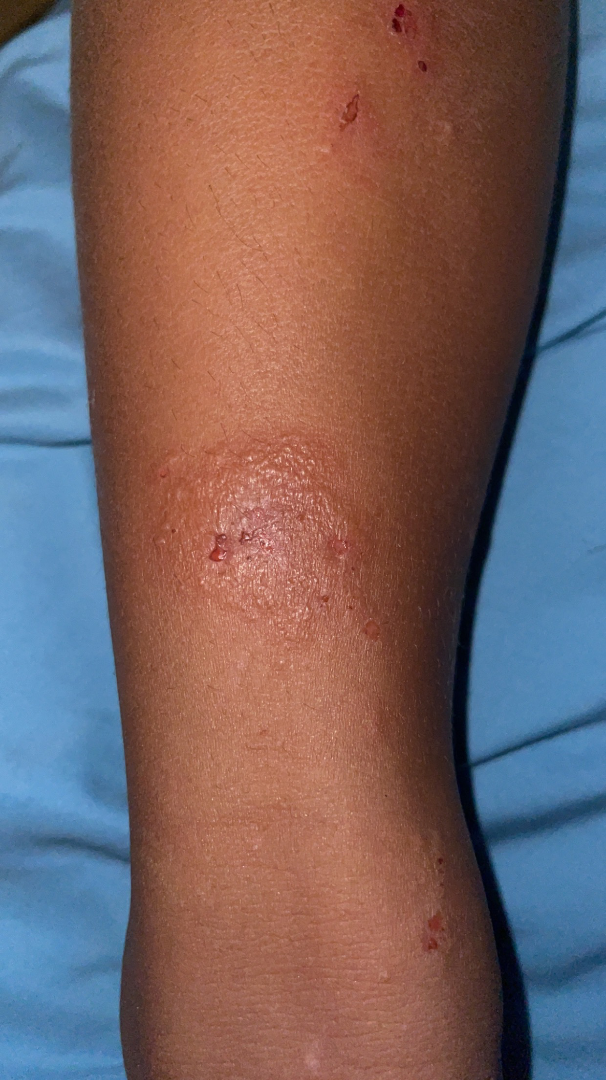On photographic review by a dermatologist, Impetigo and Allergic Contact Dermatitis were considered with similar weight; lower on the differential is Eczema.